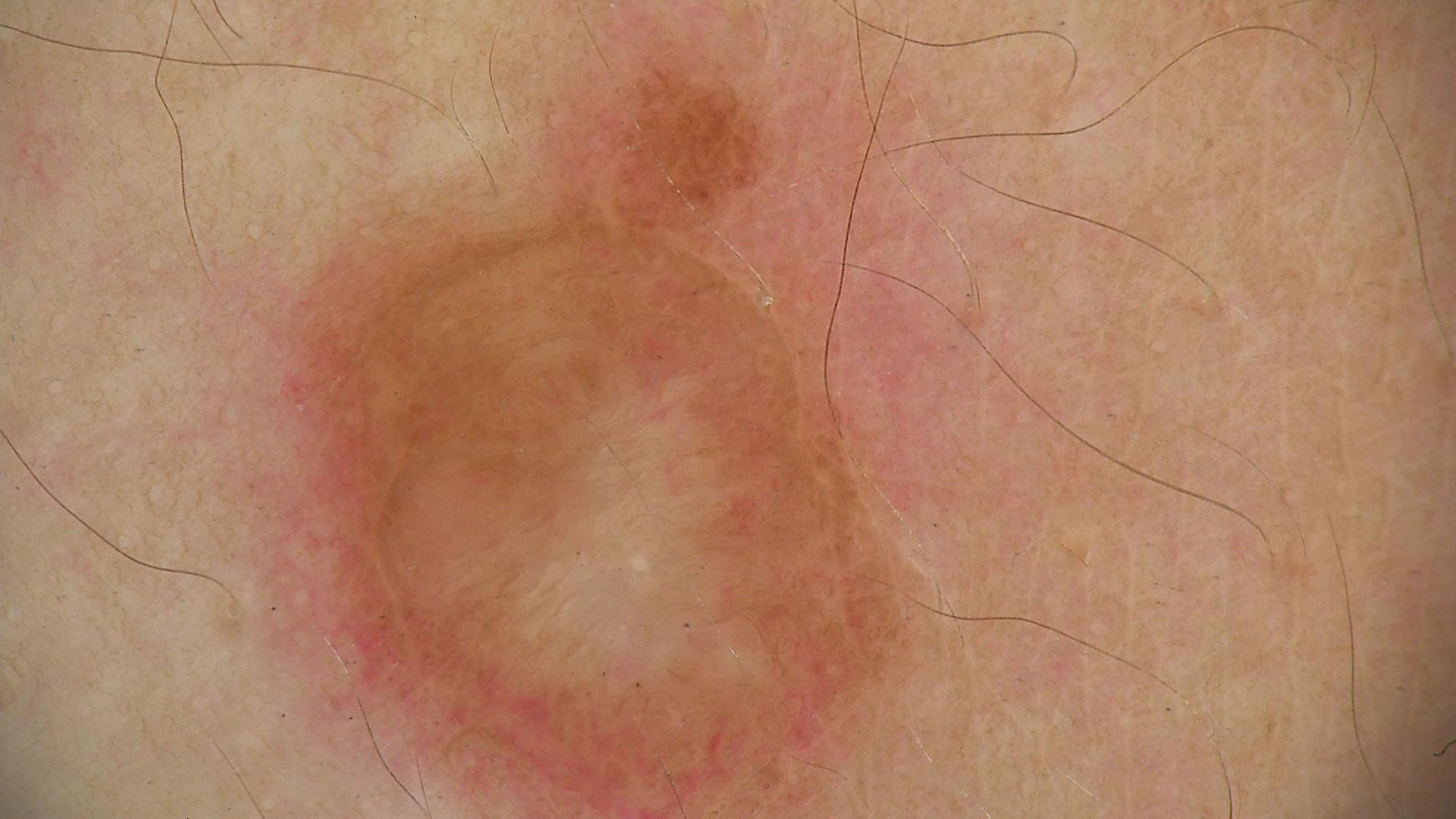Q: What kind of image is this?
A: dermatoscopy
Q: What is the diagnosis?
A: dermal nevus (expert consensus)